The affected area is the leg; this is a close-up image; the subject is 18–29, male:
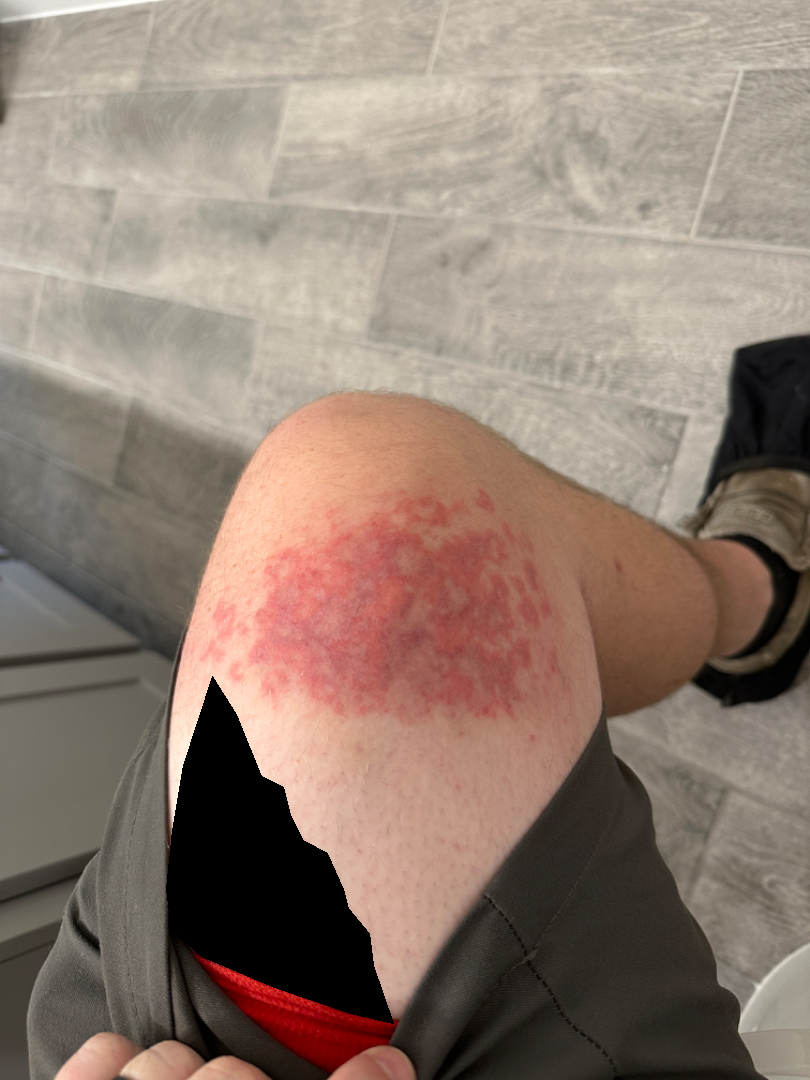{"assessment": "indeterminate", "systemic_symptoms": "mouth sores", "texture": ["raised or bumpy", "rough or flaky"]}